A clinical photograph of a skin lesion.
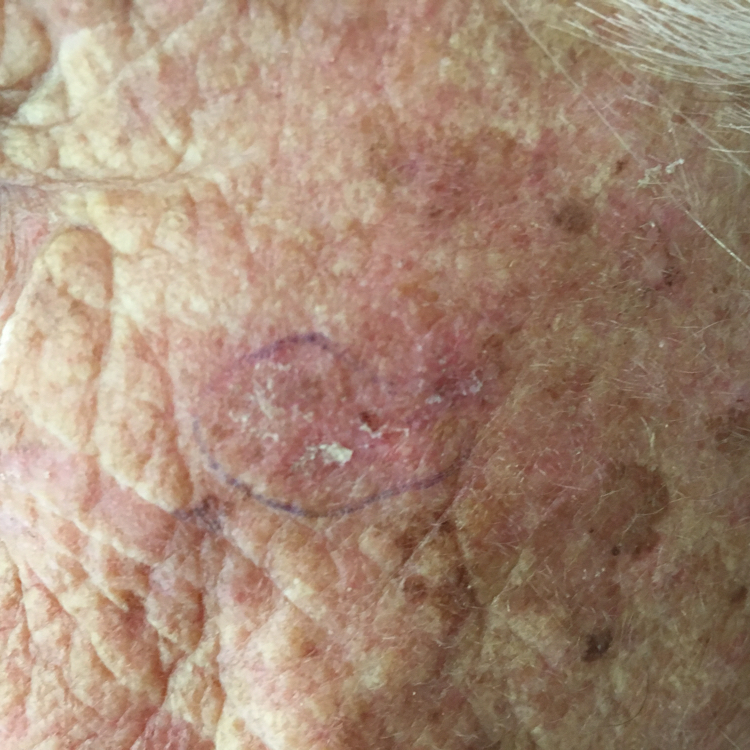{"lesion_location": "the face", "symptoms": {"present": ["itching"]}, "diagnosis": {"name": "actinic keratosis", "code": "ACK", "malignancy": "indeterminate", "confirmation": "clinical consensus"}}